This image was taken at an angle. The affected area is the leg — 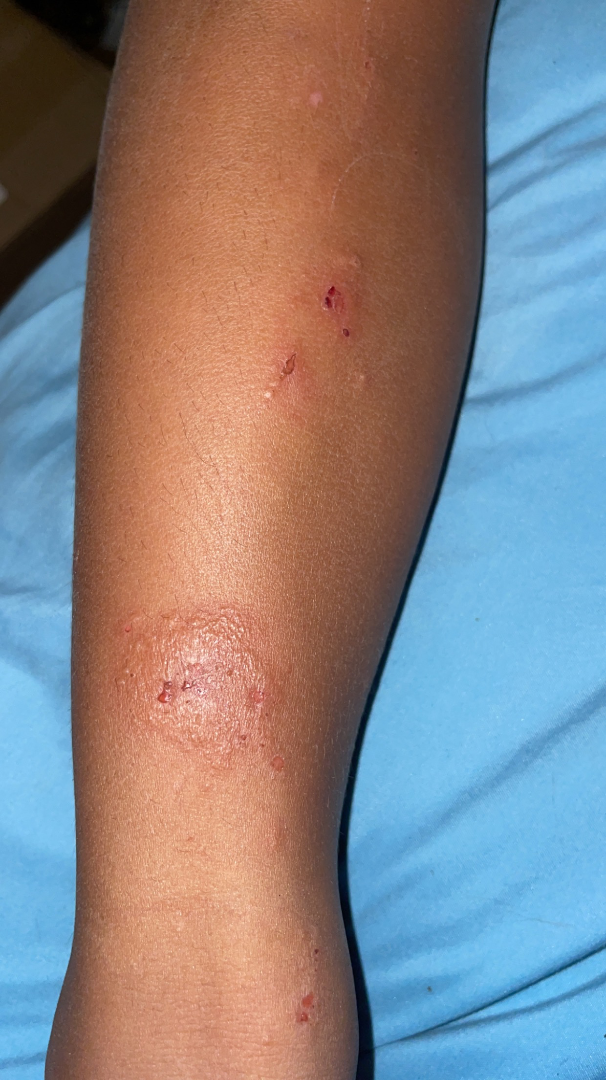Q: Reported symptoms?
A: itching
Q: Any systemic symptoms?
A: none reported
Q: How long has this been present?
A: less than one week
Q: What is the lesion texture?
A: raised or bumpy
Q: What is the dermatologist's impression?
A: Impetigo (weight 0.41); Allergic Contact Dermatitis (weight 0.41); Eczema (weight 0.18)